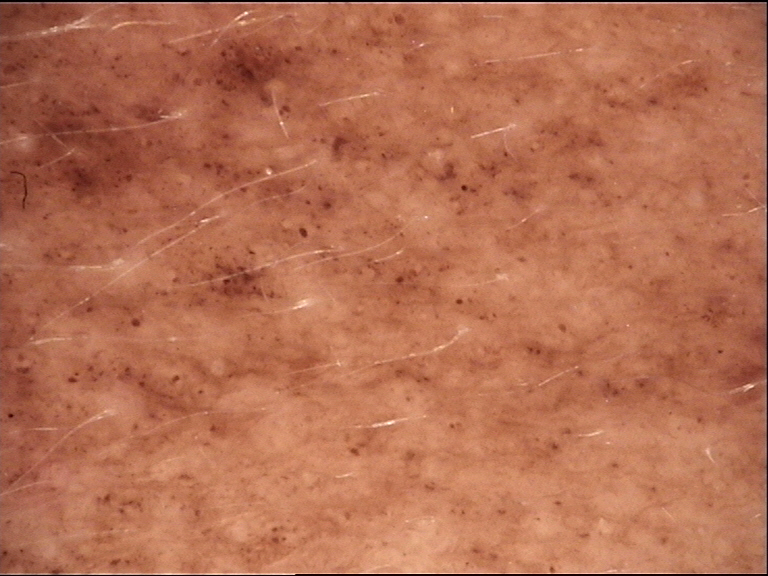Summary:
Dermoscopy of a skin lesion. This is a banal lesion.
Conclusion:
The diagnostic label was a congenital junctional nevus.